A skin lesion imaged with a dermatoscope.
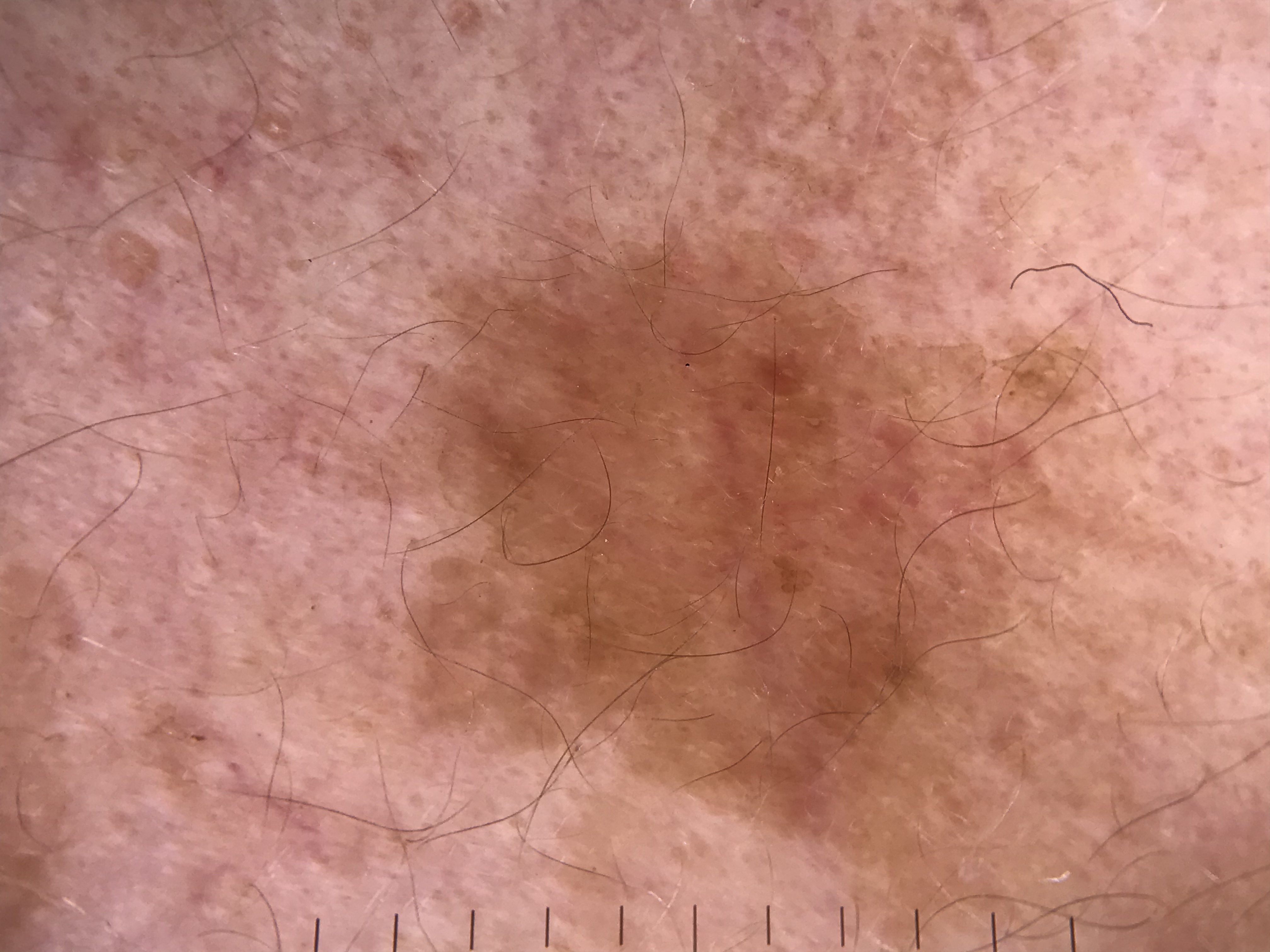The architecture is that of a keratinocytic lesion. The diagnosis was a benign lesion — a seborrheic keratosis.